A dermoscopic photograph of a skin lesion.
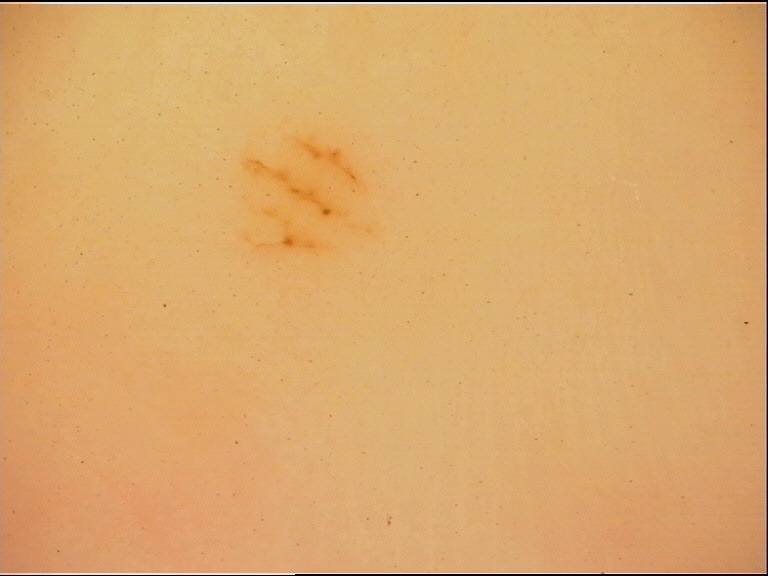The architecture is that of a banal lesion. The diagnosis was an acral junctional nevus.